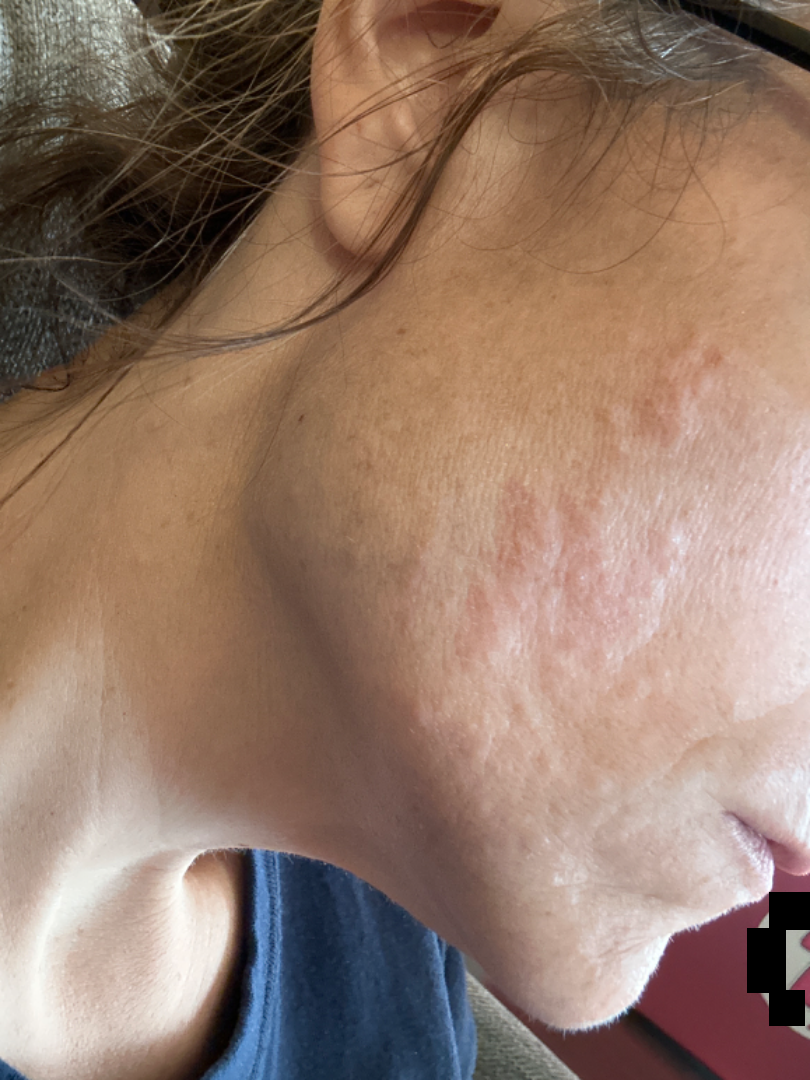No differential diagnosis could be assigned on photographic review.
A close-up photograph.